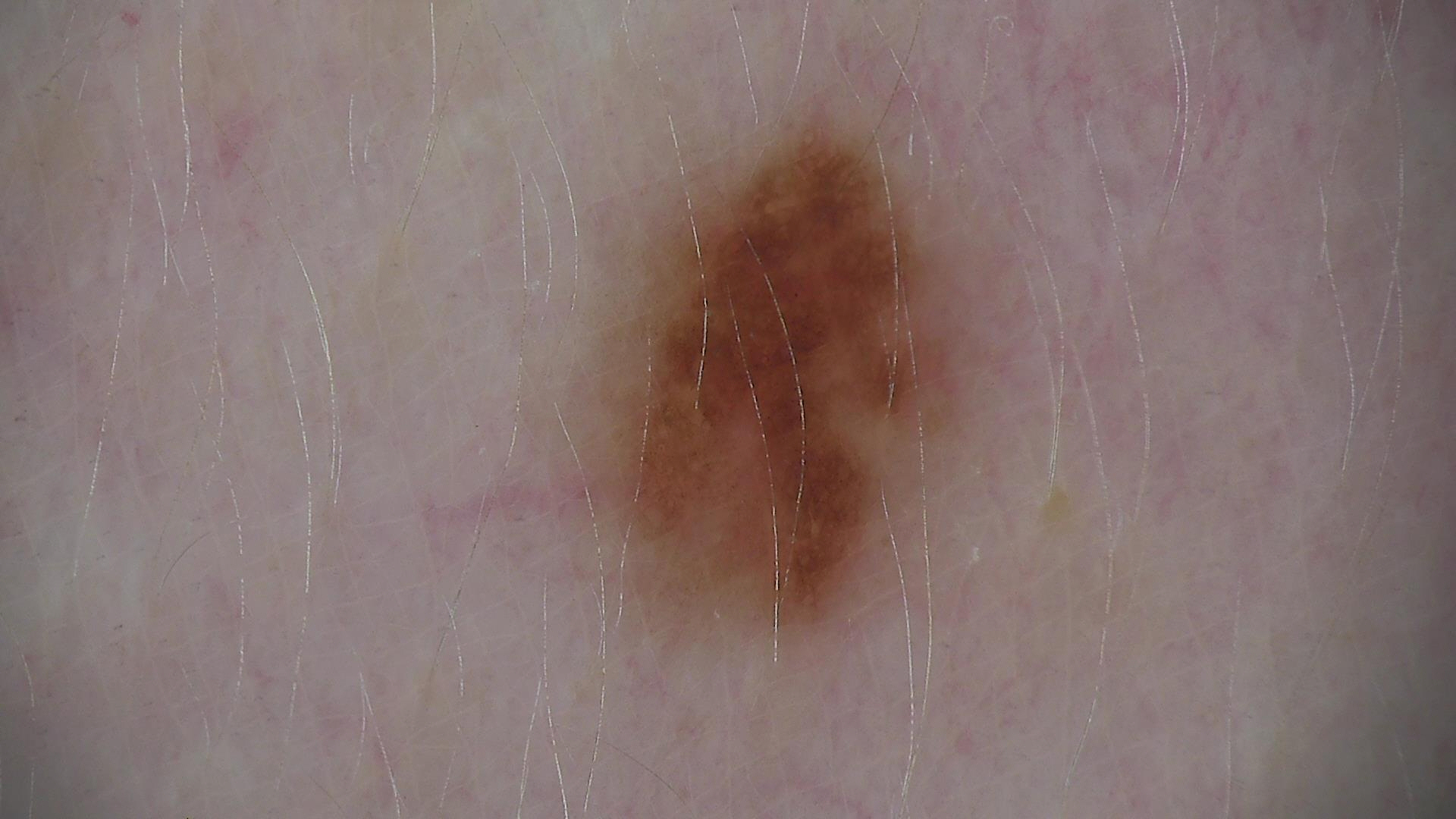Impression:
Classified as a dysplastic junctional nevus.